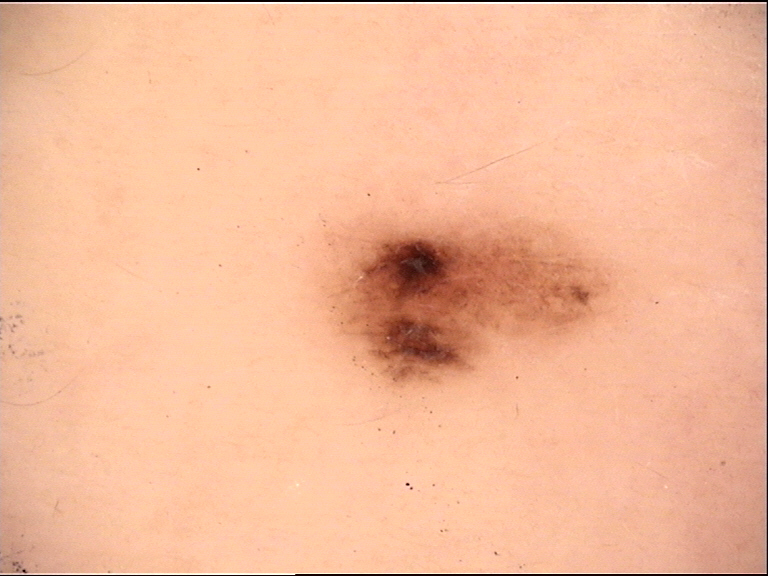Q: What kind of image is this?
A: dermoscopy
Q: What was the diagnostic impression?
A: dysplastic junctional nevus (expert consensus)